A dermoscopic image of a skin lesion: 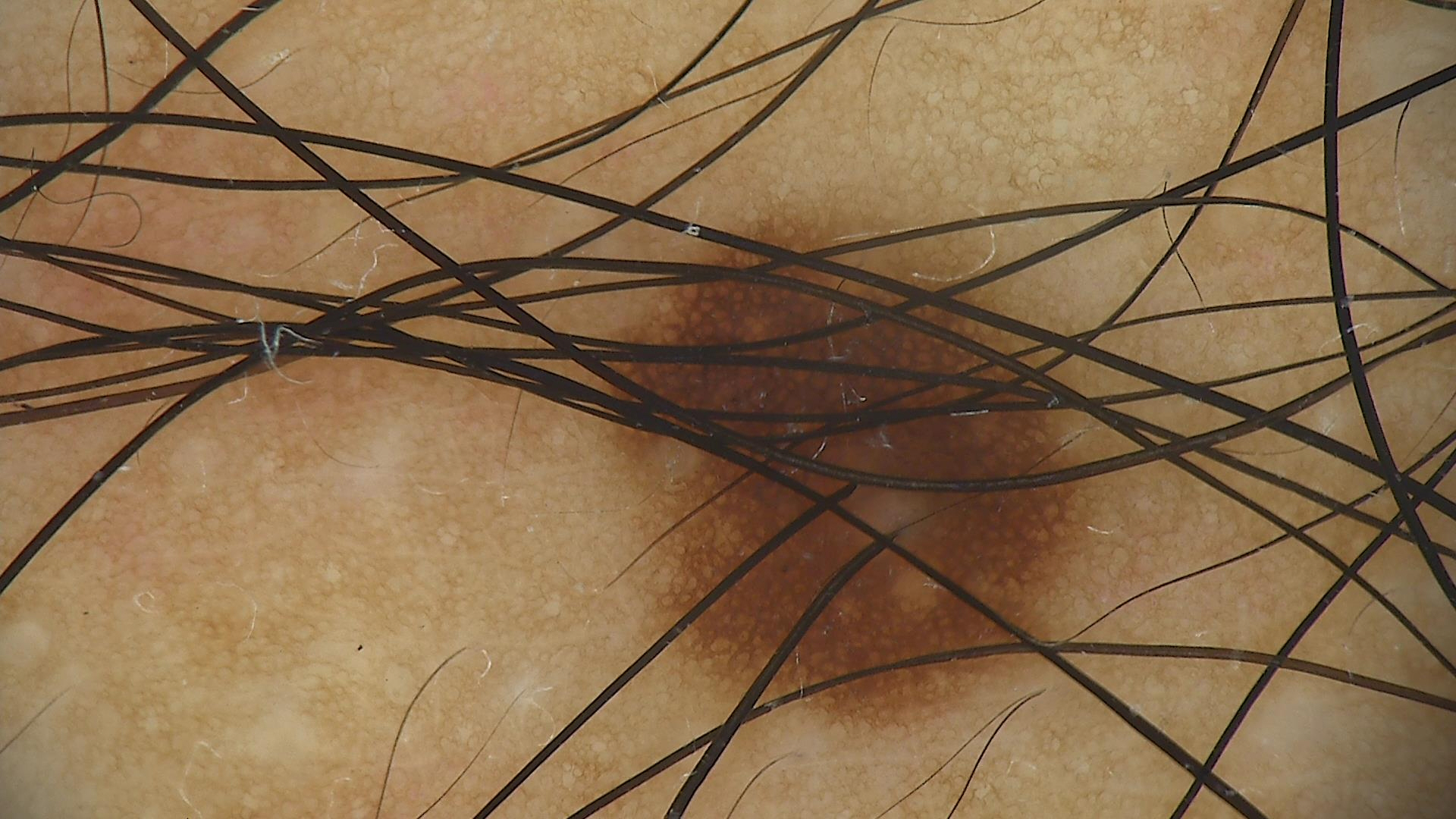Diagnosed as a benign lesion — a dysplastic junctional nevus.